A dermatoscopic image of a skin lesion: 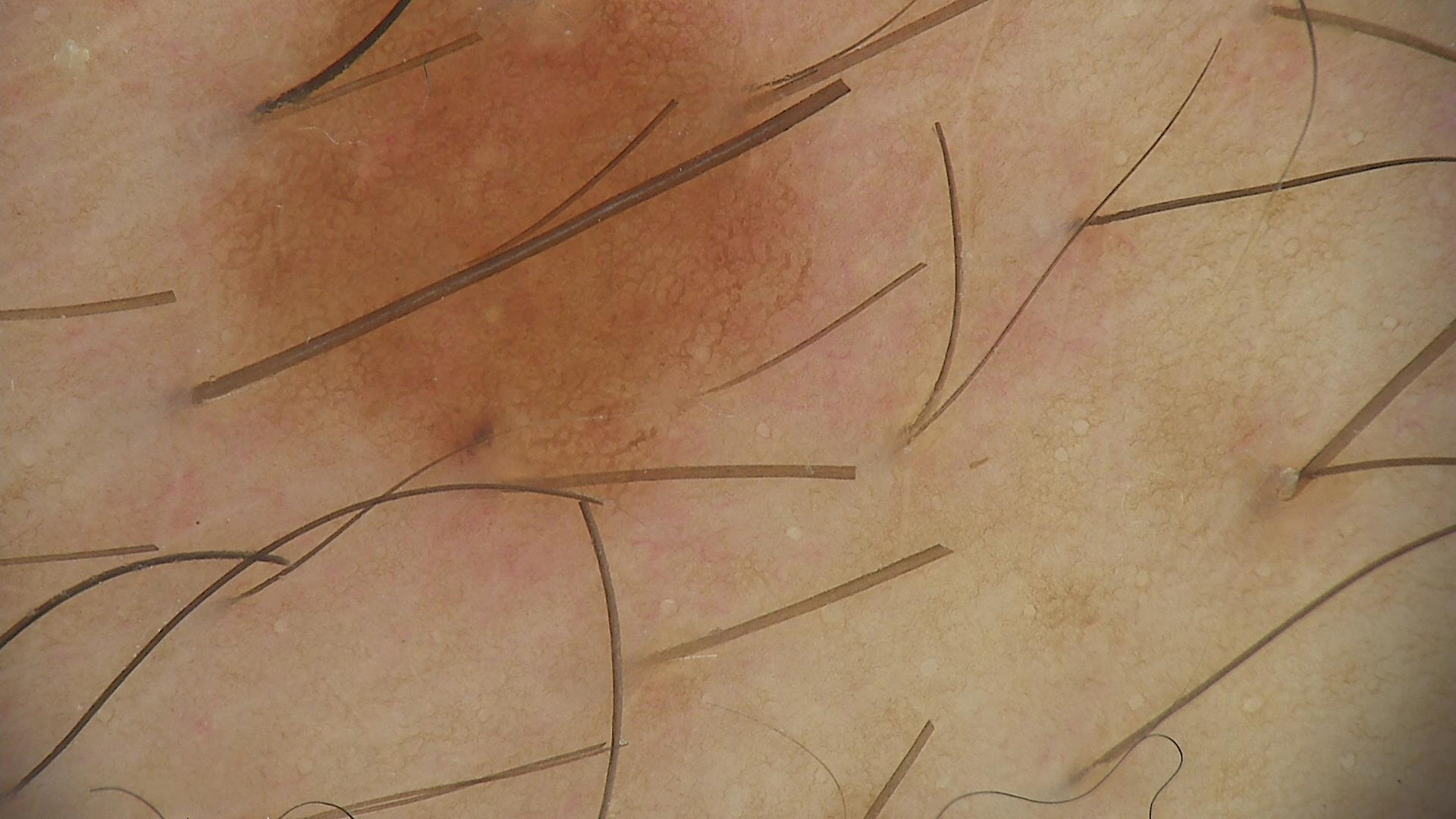This is a banal lesion.
The diagnosis was a junctional nevus.